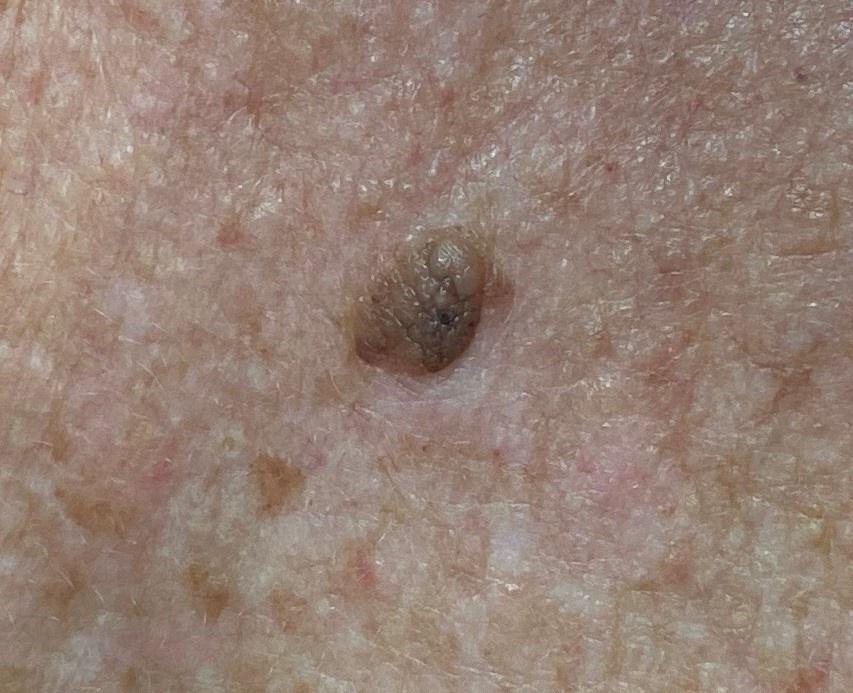The chart documents a previous melanoma. An overview clinical photograph of a skin lesion. Located on the trunk. Histopathological examination showed a benign lesion — a seborrheic keratosis.